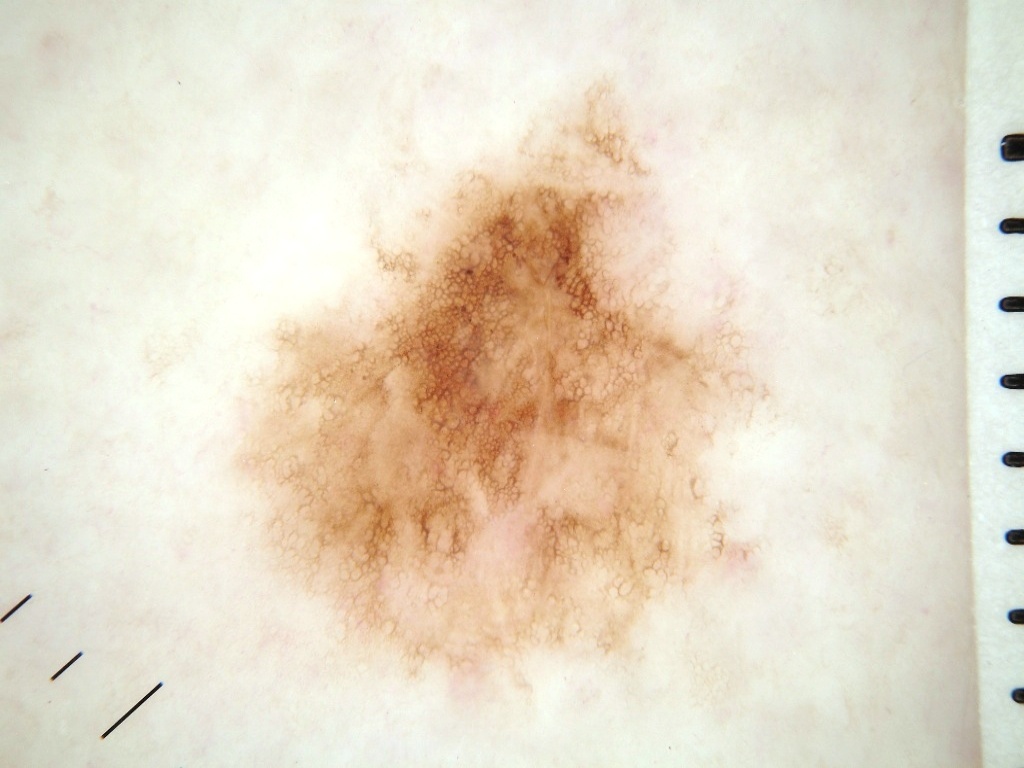{"image": {"modality": "dermoscopy"}, "patient": {"sex": "female", "age_approx": "85+"}, "dermoscopic_features": {"present": ["pigment network"], "absent": ["milia-like cysts", "globules", "streaks", "negative network"]}, "lesion_extent": {"approx_field_fraction_pct": 25}, "lesion_location": {"bbox_xyxy": [233, 78, 770, 698]}, "diagnosis": {"name": "melanocytic nevus", "malignancy": "benign", "lineage": "melanocytic", "provenance": "clinical"}}